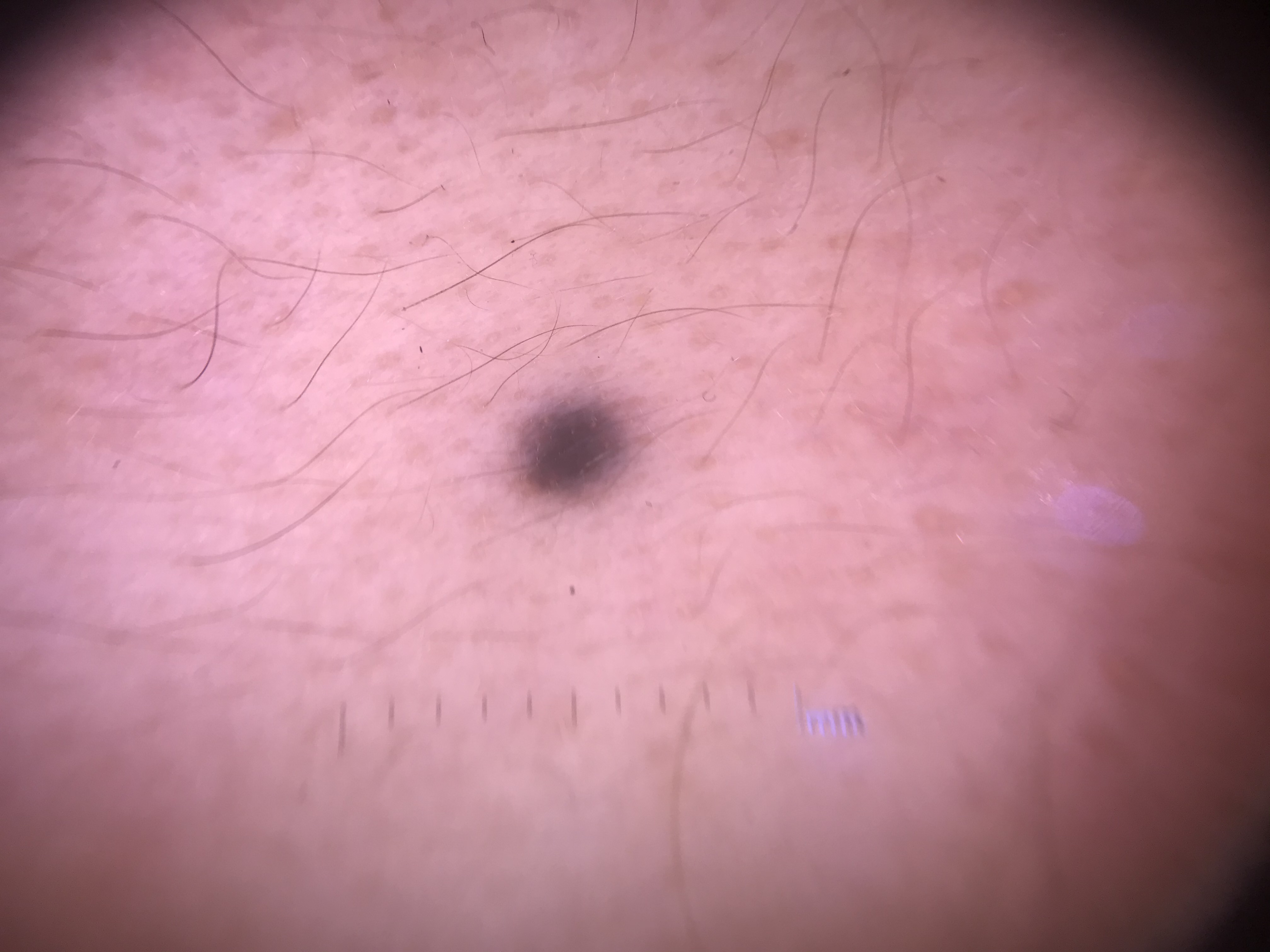Summary: A dermoscopic close-up of a skin lesion. Conclusion: Labeled as a dermal lesion — a blue nevus.